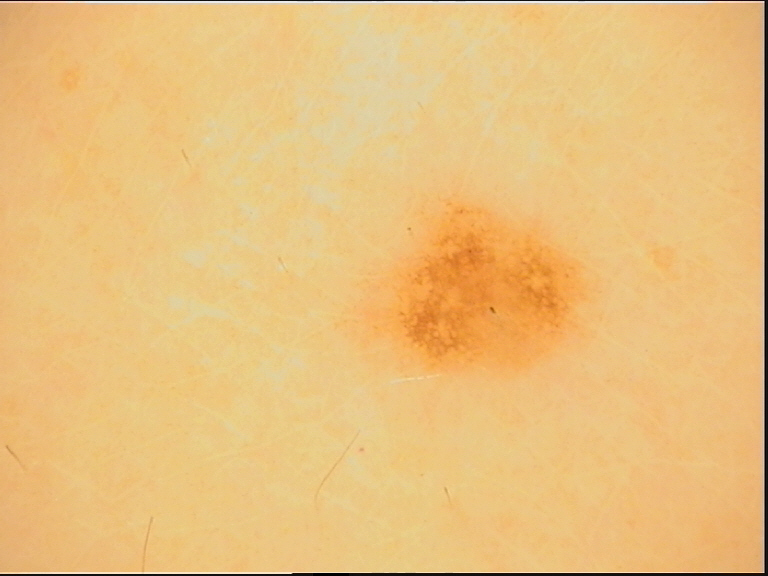Q: What is the diagnosis?
A: dysplastic junctional nevus (expert consensus)